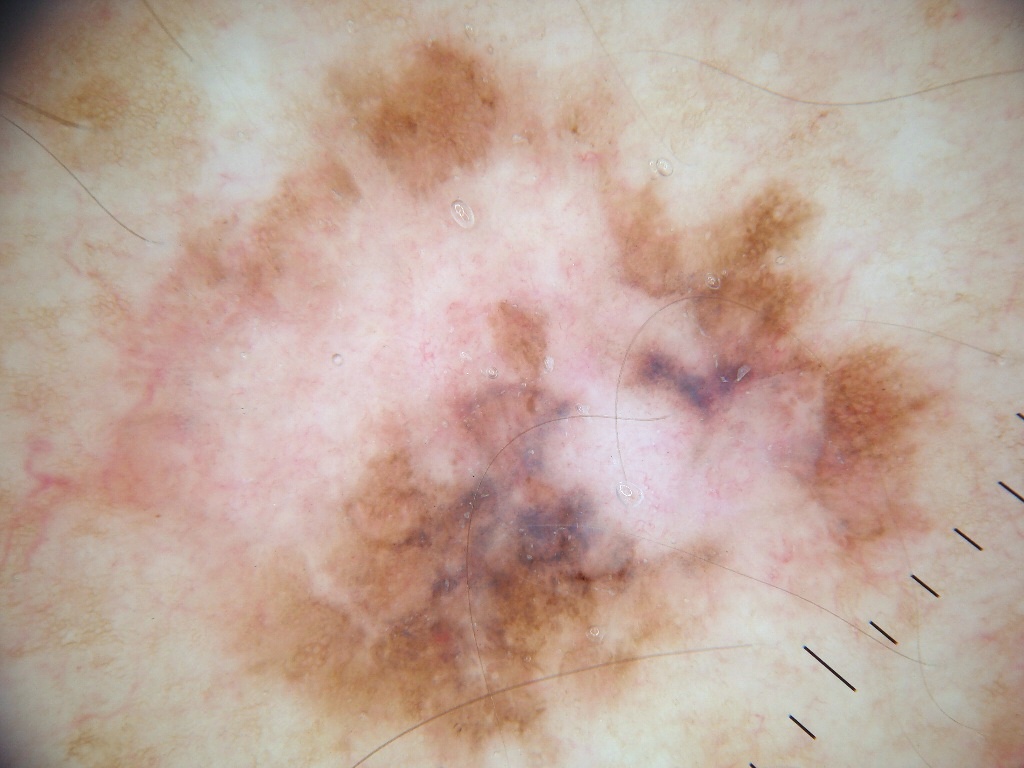| key | value |
|---|---|
| modality | dermoscopic image |
| patient | male, aged 58 to 62 |
| dermoscopic pattern | pigment network and negative network; absent: globules, streaks, and milia-like cysts |
| lesion size | ~65% of the field |
| bounding box | 39 30 958 766 |
| diagnosis | a melanoma |